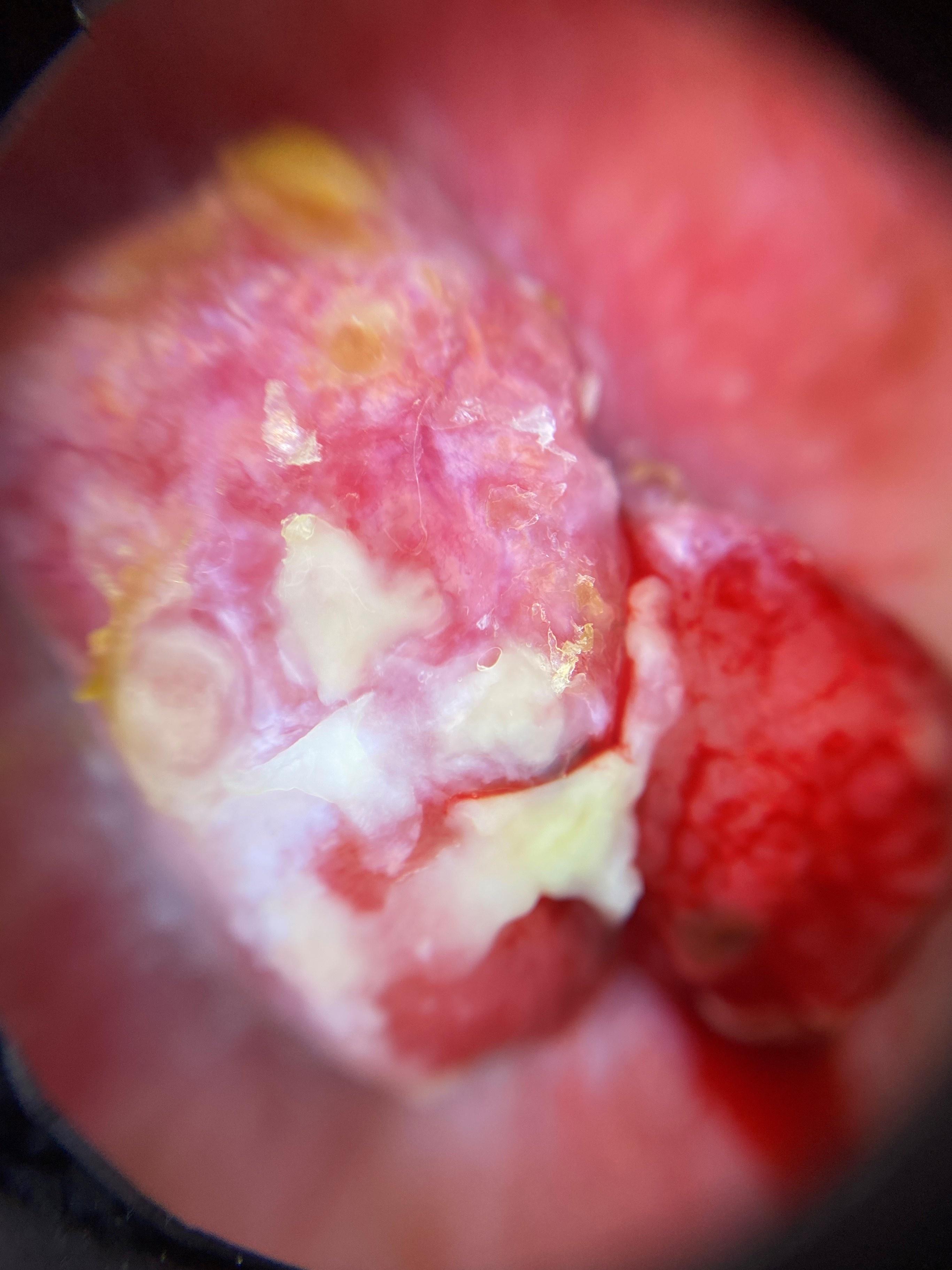Q: What is this lesion?
A: Melanoma (biopsy-proven)